A dermoscopic image of a skin lesion.
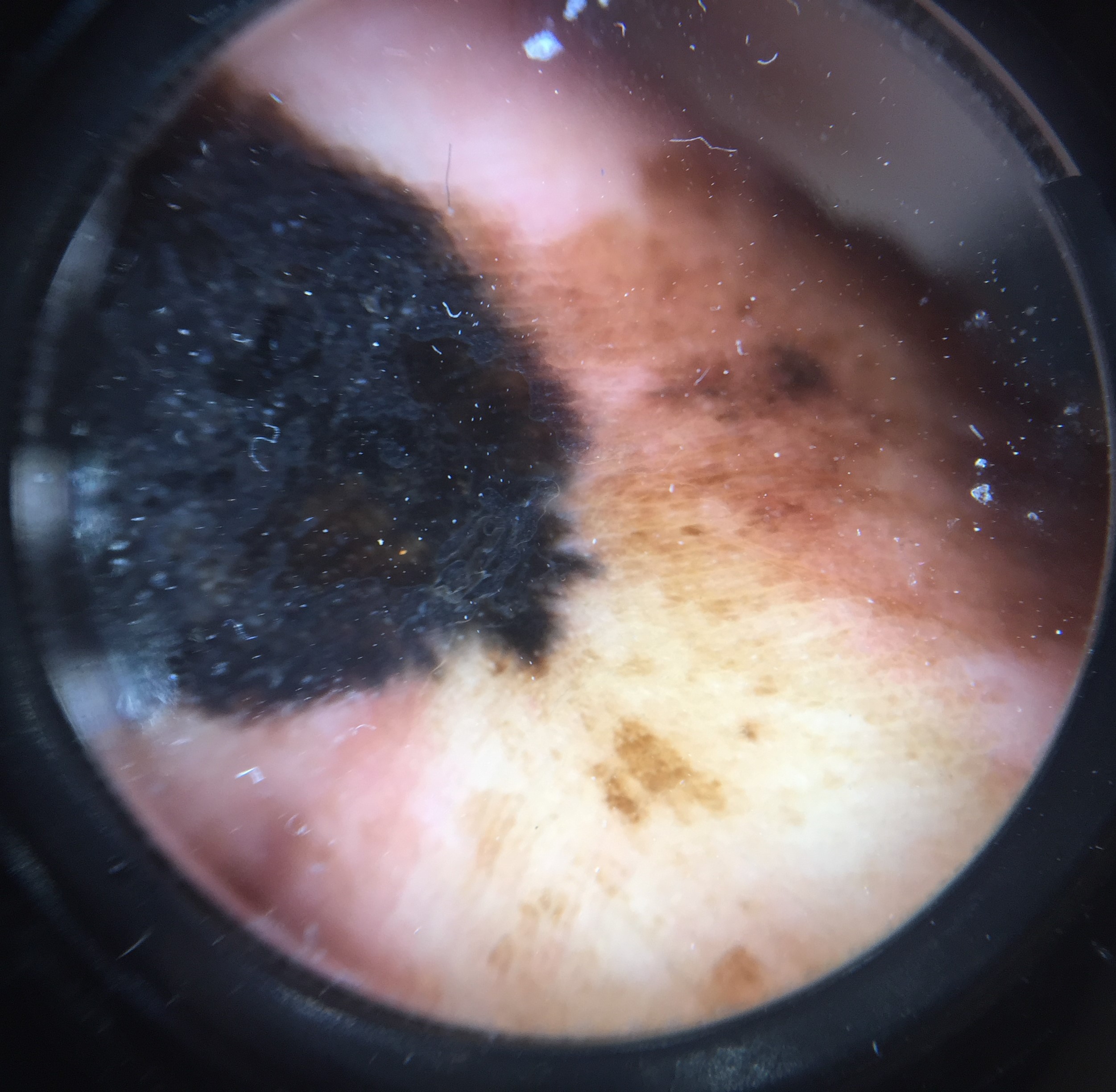Case:
- class · acral lentiginous melanoma (biopsy-proven)